Dermoscopy of a skin lesion: 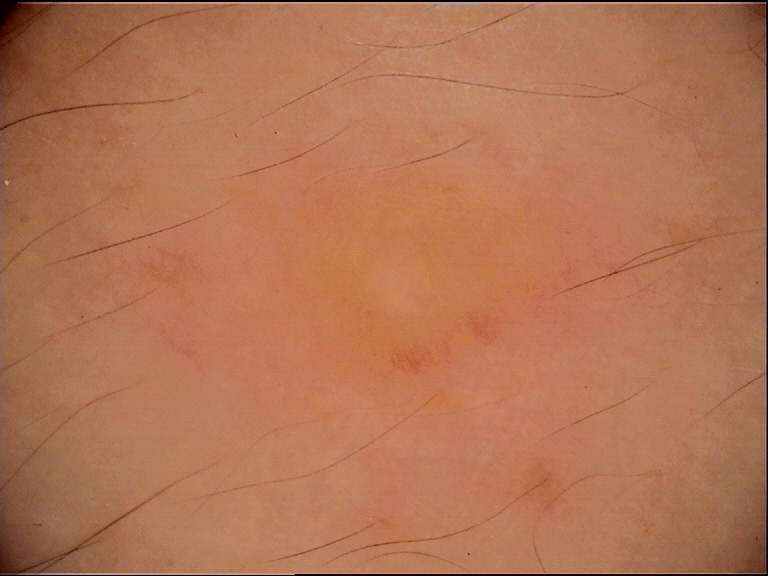diagnosis:
  name: dermatofibroma
  code: df
  malignancy: benign
  super_class: non-melanocytic
  confirmation: expert consensus